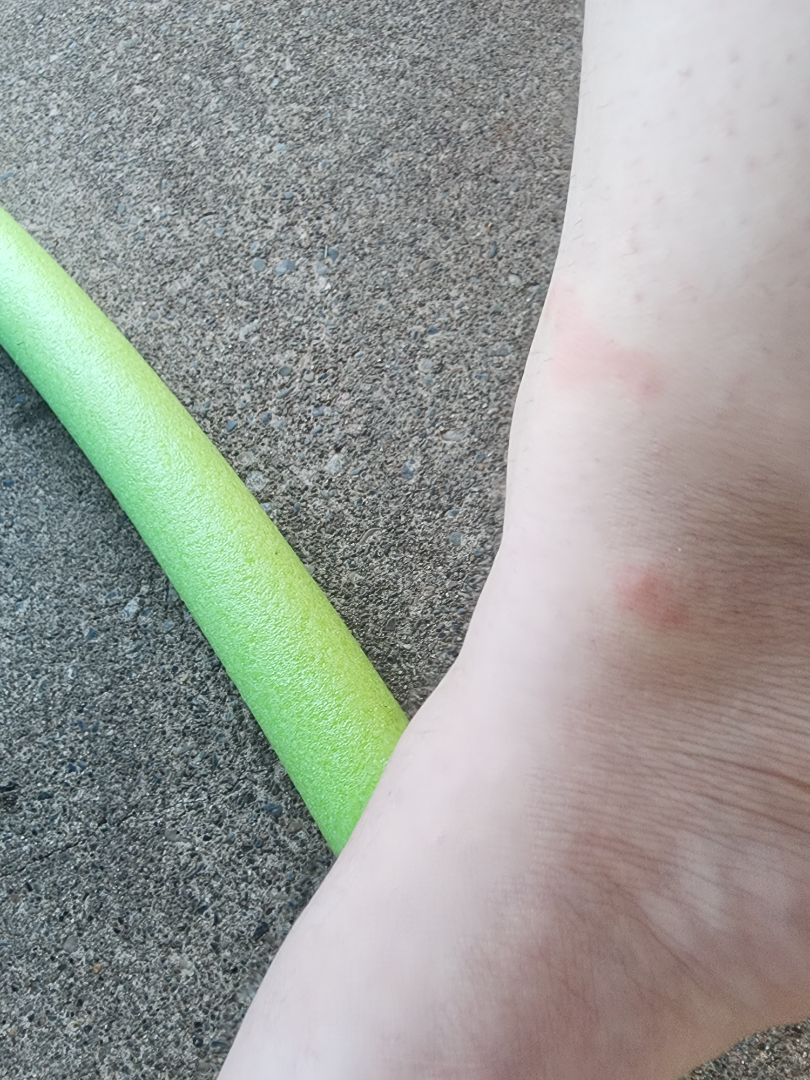No differential diagnosis could be assigned on photographic review.
The top or side of the foot is involved.
The photograph was taken at an angle.